A female patient, aged 63 to 67; a dermoscopic image of a skin lesion — 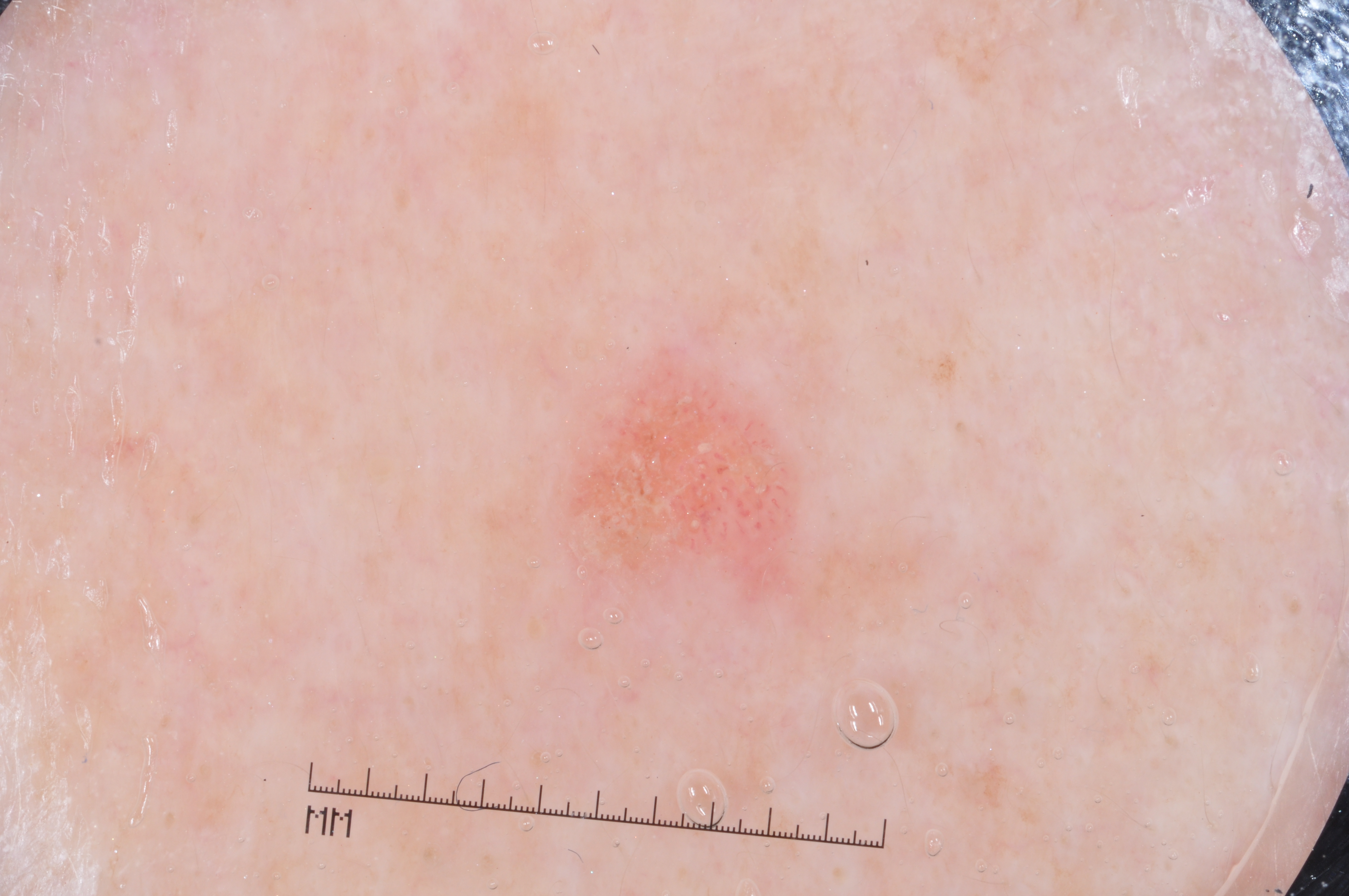{"dermoscopic_features": {"present": ["milia-like cysts"], "absent": ["streaks", "pigment network", "negative network"]}, "lesion_extent": "small", "lesion_location": {"bbox_xyxy": [559, 365, 811, 595]}, "diagnosis": {"name": "seborrheic keratosis", "malignancy": "benign", "lineage": "keratinocytic", "provenance": "clinical"}}